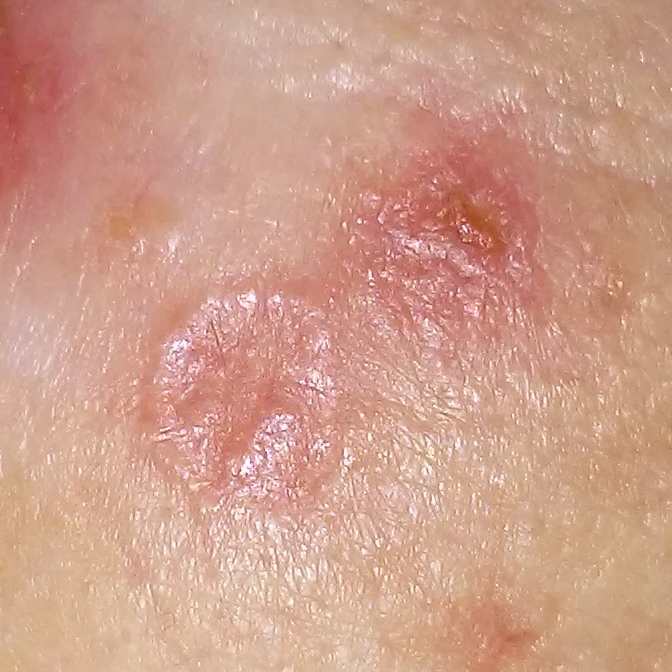risk_factors:
  positive:
    - prior skin cancer (patient or family)
skin_type: I
patient:
  age: 51
  gender: female
lesion_size:
  diameter_1_mm: 25.0
  diameter_2_mm: 11.0
symptoms:
  present:
    - itching
    - growth
    - bleeding
diagnosis:
  name: basal cell carcinoma
  code: BCC
  malignancy: malignant
  confirmation: histopathology